The patient described the issue as a rash. Present for about one day. The contributor is 30–39, female. Close-up view. Texture is reported as rough or flaky. Reported lesion symptoms include bothersome appearance. The affected area is the head or neck — 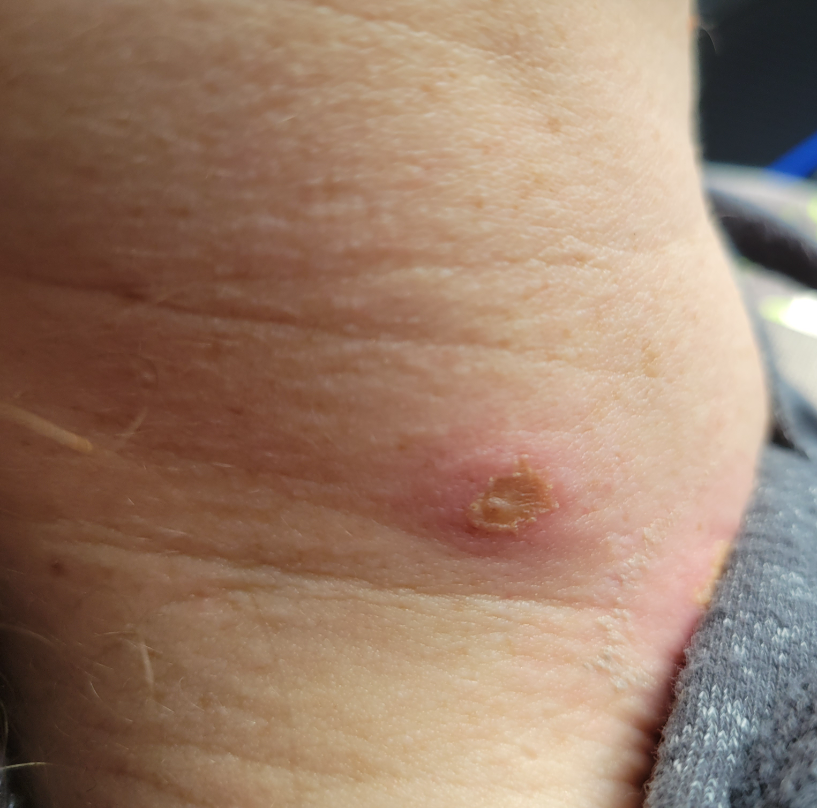Assessment: The reviewing dermatologist was unable to assign a differential diagnosis from the image.